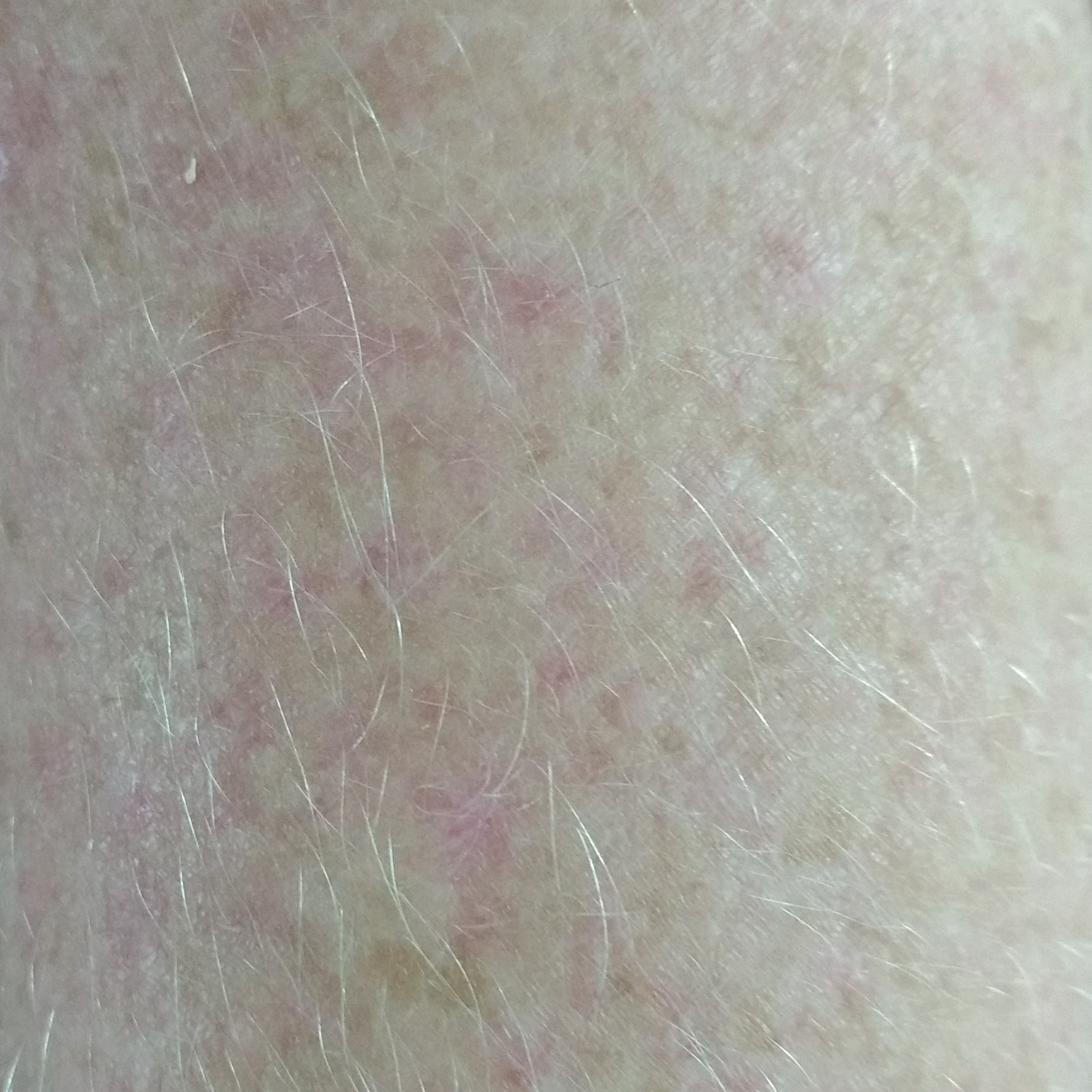<lesion>
  <image>clinical photo</image>
  <patient>
    <age>47</age>
  </patient>
  <lesion_location>a forearm</lesion_location>
  <symptoms>
    <present>itching</present>
    <absent>elevation</absent>
  </symptoms>
  <diagnosis>
    <name>actinic keratosis</name>
    <code>ACK</code>
    <malignancy>indeterminate</malignancy>
    <confirmation>clinical consensus</confirmation>
  </diagnosis>
</lesion>